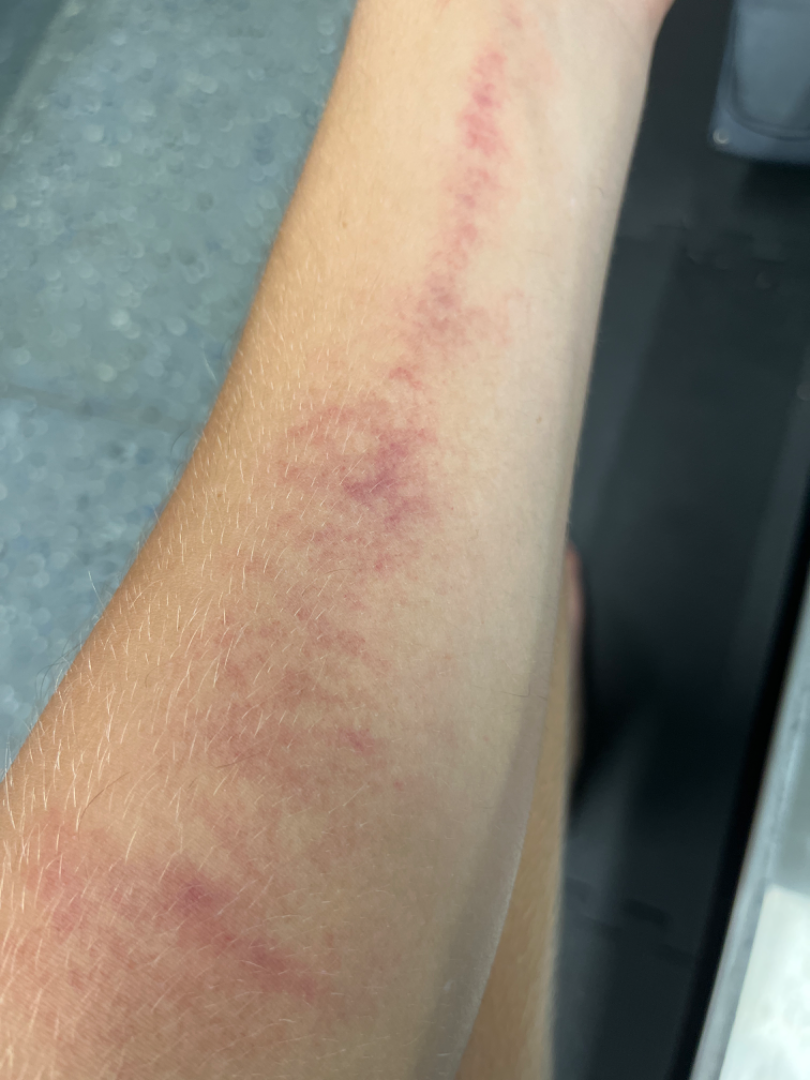assessment: ungradable on photographic review | site: arm | shot type: close-up.